Close-up view; female patient, age 18–29; located on the back of the hand:
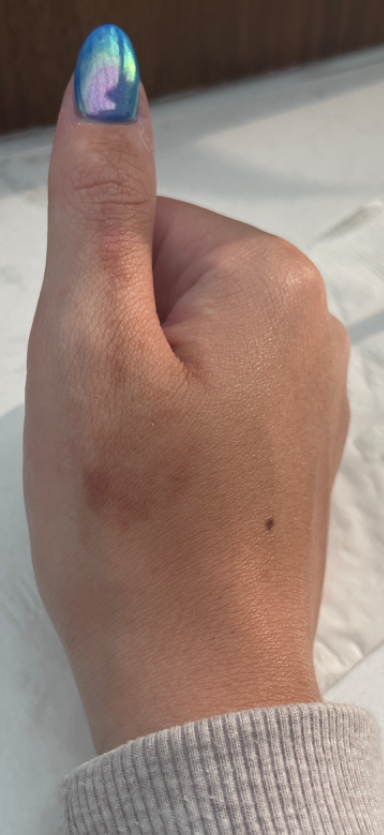<report>
  <differential>
    <leading>Photodermatitis</leading>
    <considered>Hyperpigmentation disorder, Post-Inflammatory hyperpigmentation</considered>
  </differential>
</report>